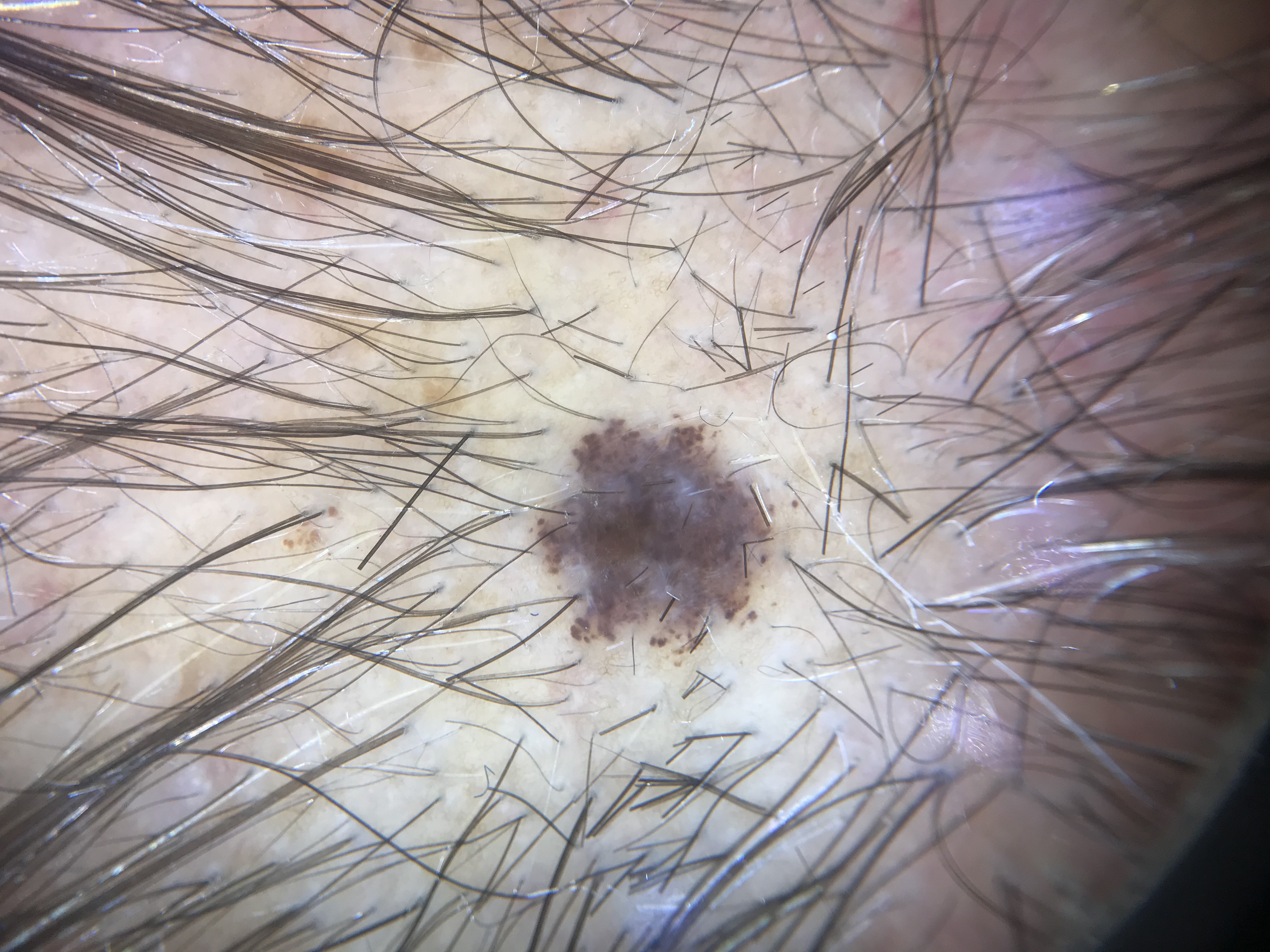Diagnosed as a dysplastic compound nevus.